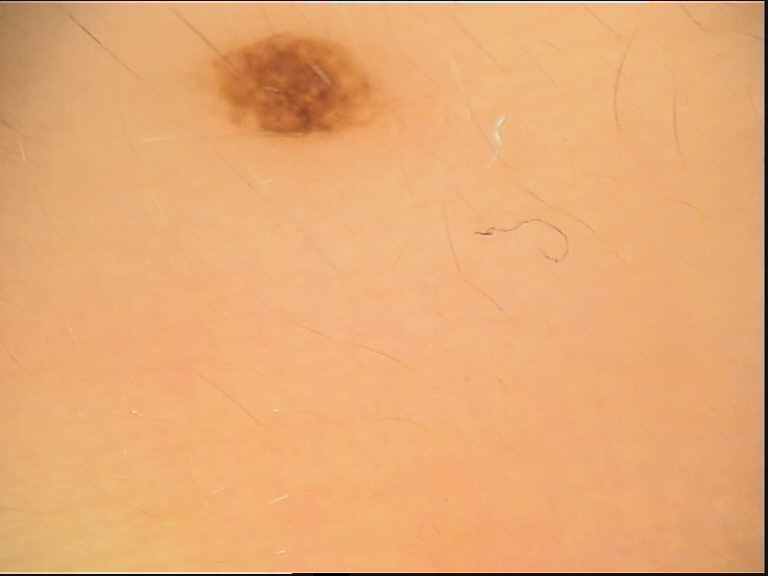Consistent with a dysplastic compound nevus.